A dermoscopy image of a single skin lesion:
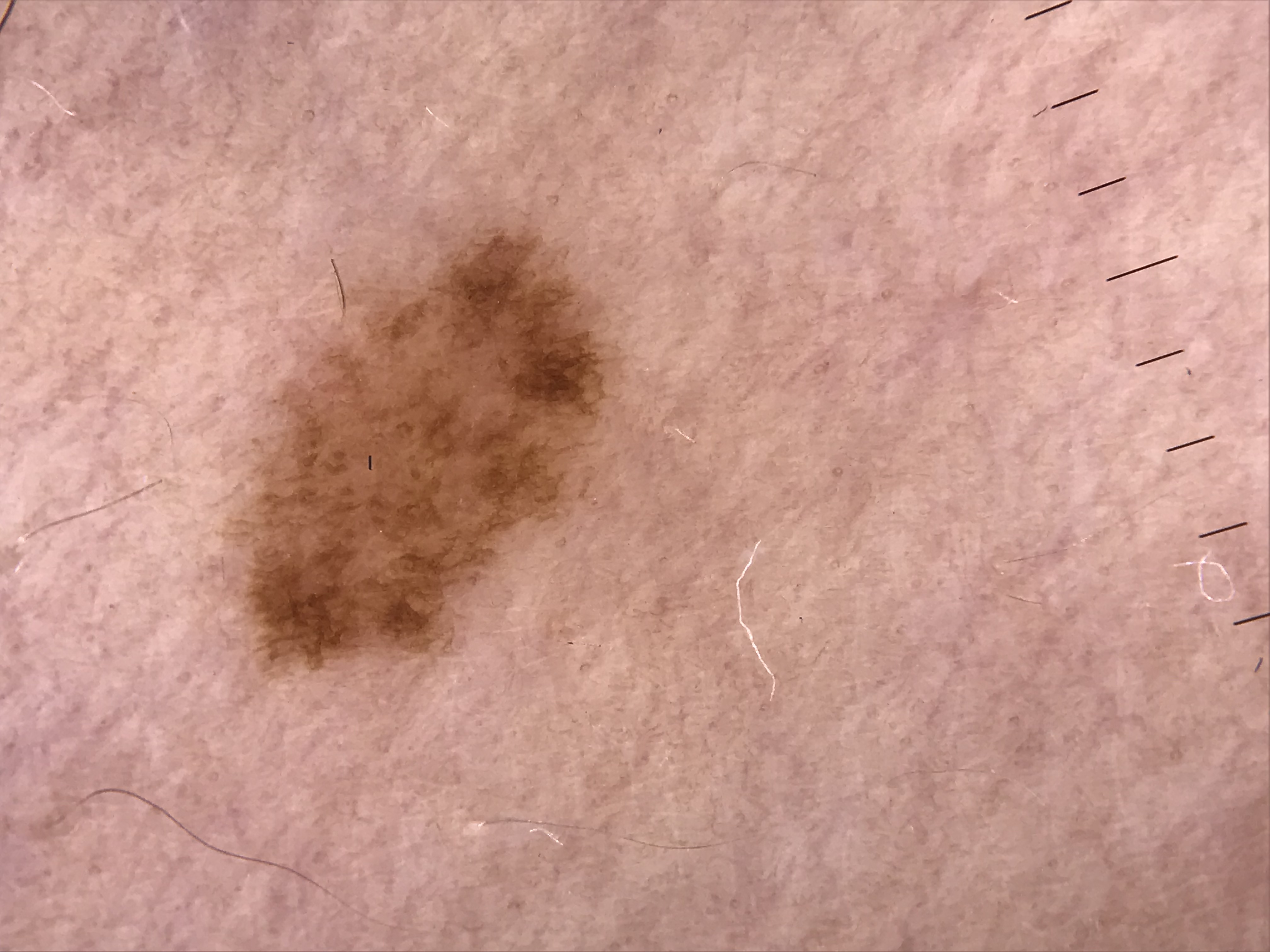The diagnostic label was a benign lesion — a dysplastic junctional nevus.